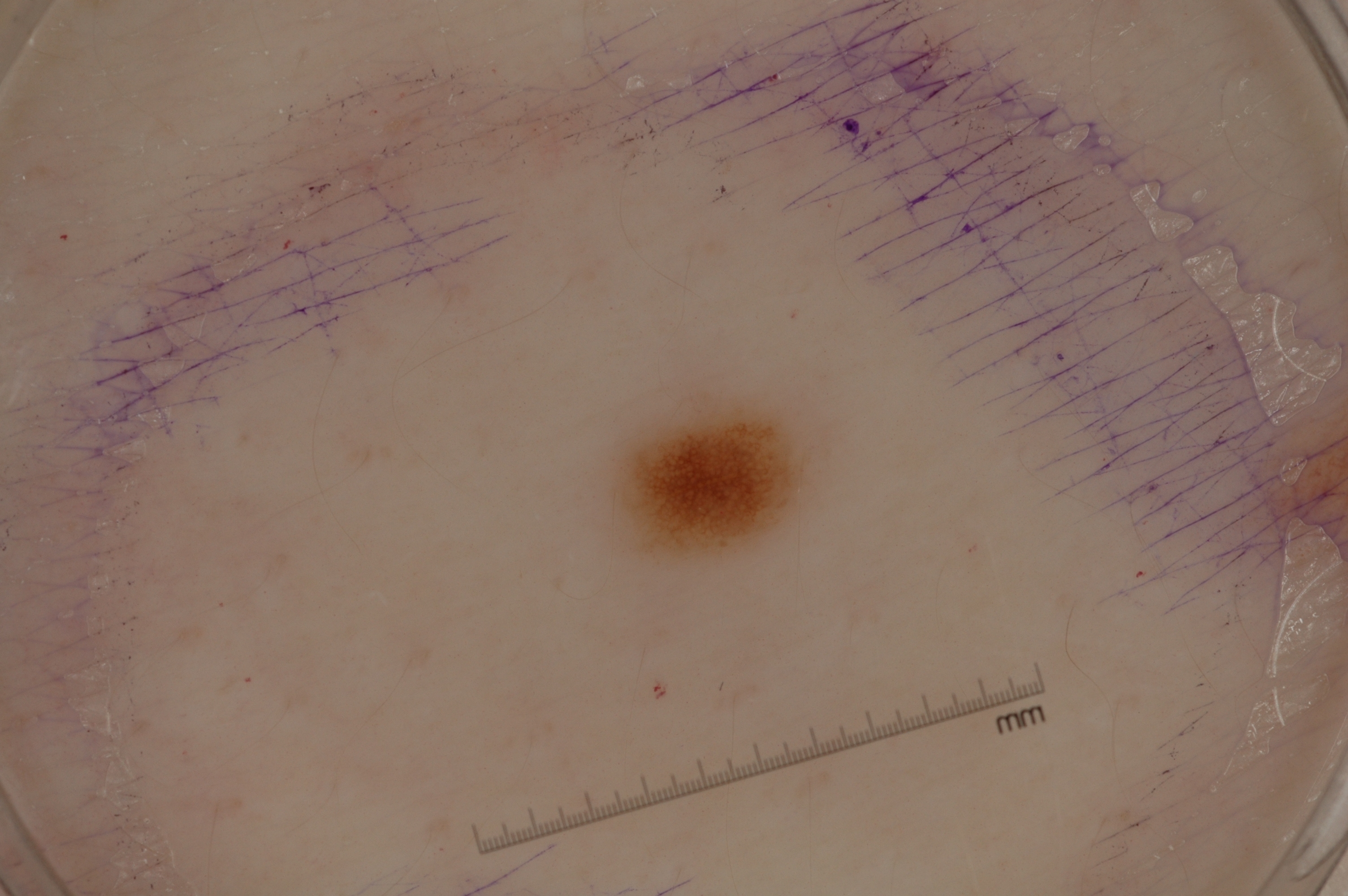Q: What kind of image is this?
A: dermatoscopic image of a skin lesion
Q: Patient demographics?
A: female, aged 28 to 32
Q: How large is the lesion within the image?
A: small
Q: What does dermoscopy show?
A: pigment network; absent: negative network, milia-like cysts, and streaks
Q: What is the lesion's bounding box?
A: 611, 399, 811, 560
Q: What did the assessment conclude?
A: a melanocytic nevus